A dermoscopic close-up of a skin lesion.
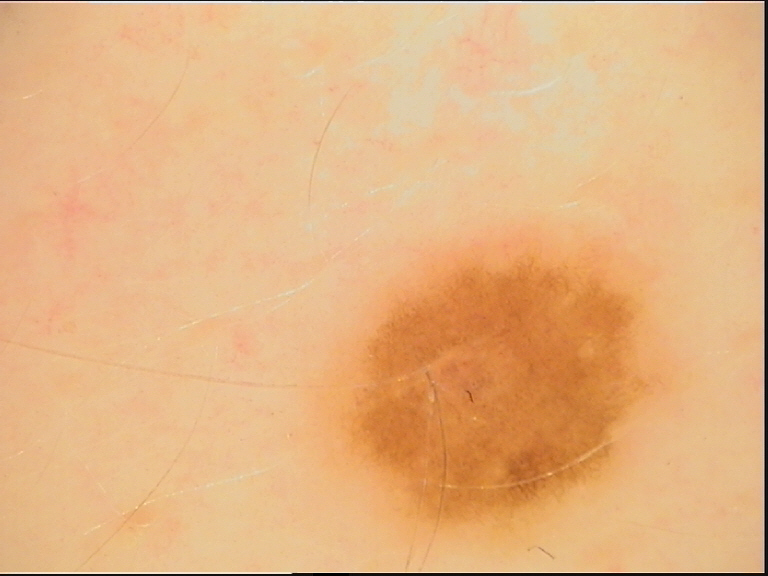Impression: The diagnosis was a benign lesion — a dysplastic junctional nevus.